Located on the arm and back of the hand. The contributor is a female aged 18–29. A close-up photograph.
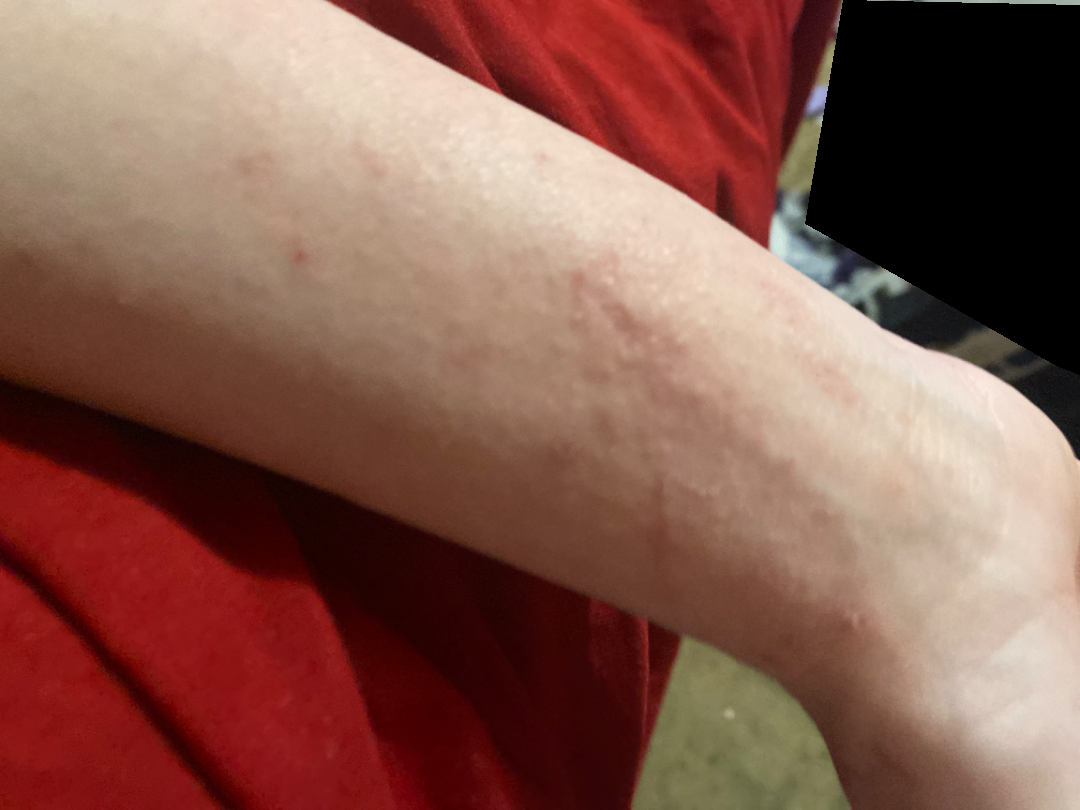History: The patient reported no systemic symptoms. The contributor reports the condition has been present for less than one week. Fitzpatrick phototype IV; non-clinician graders estimated 2 on the Monk Skin Tone. The lesion is described as raised or bumpy. The patient considered this a rash. Impression: On photographic review by a dermatologist: favoring Eczema; an alternative is Allergic Contact Dermatitis.